The patient reports the condition has been present for one to three months · the leg is involved · the lesion is described as flat · the patient is 18–29, female · reported lesion symptoms include darkening and bothersome appearance · the photograph is a close-up of the affected area · the patient reports associated fatigue: 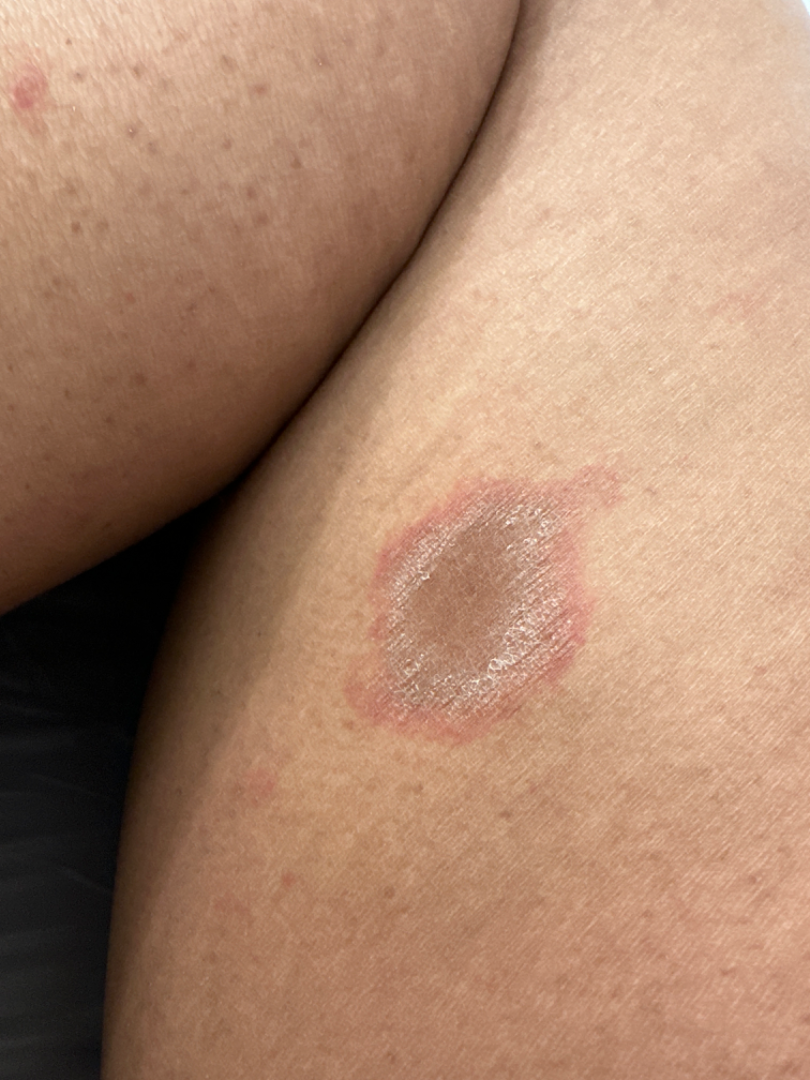diagnostic considerations=the impression is Drug Rash